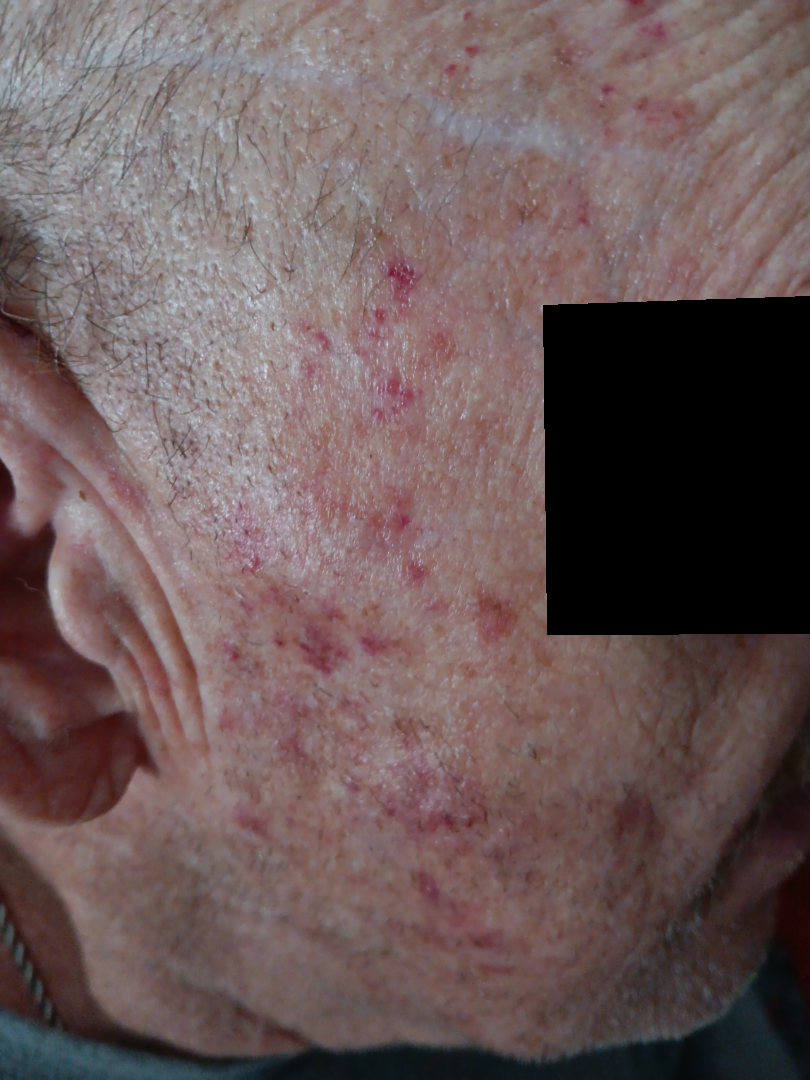The reviewing dermatologist was unable to assign a differential diagnosis from the image.